A female subject approximately 70 years of age; a dermoscopy image of a single skin lesion:
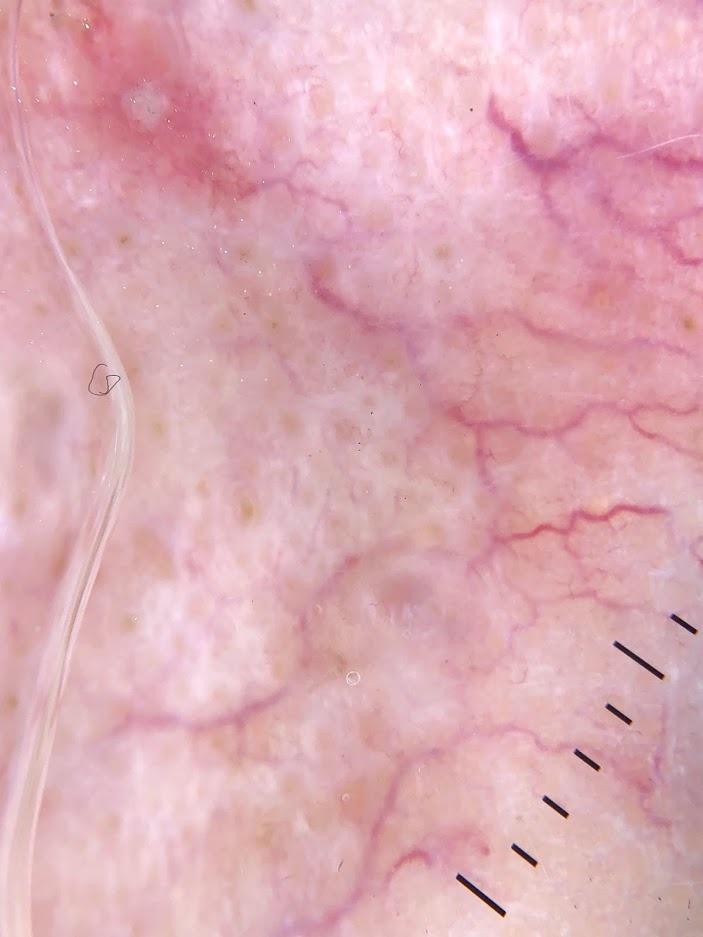Case:
* diagnosis · Basal cell carcinoma (biopsy-proven)